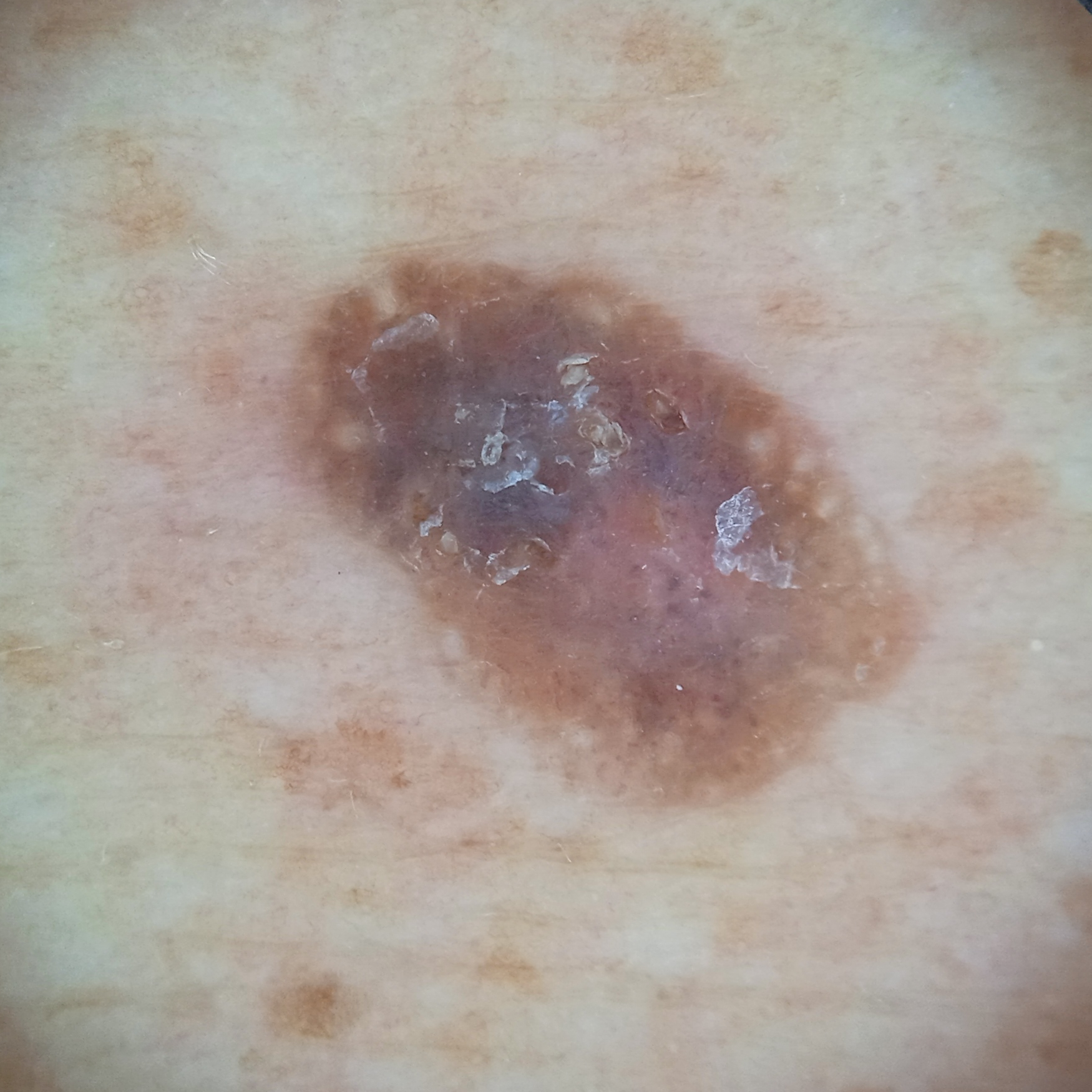  diagnosis:
    name: seborrheic keratosis
    malignancy: benign